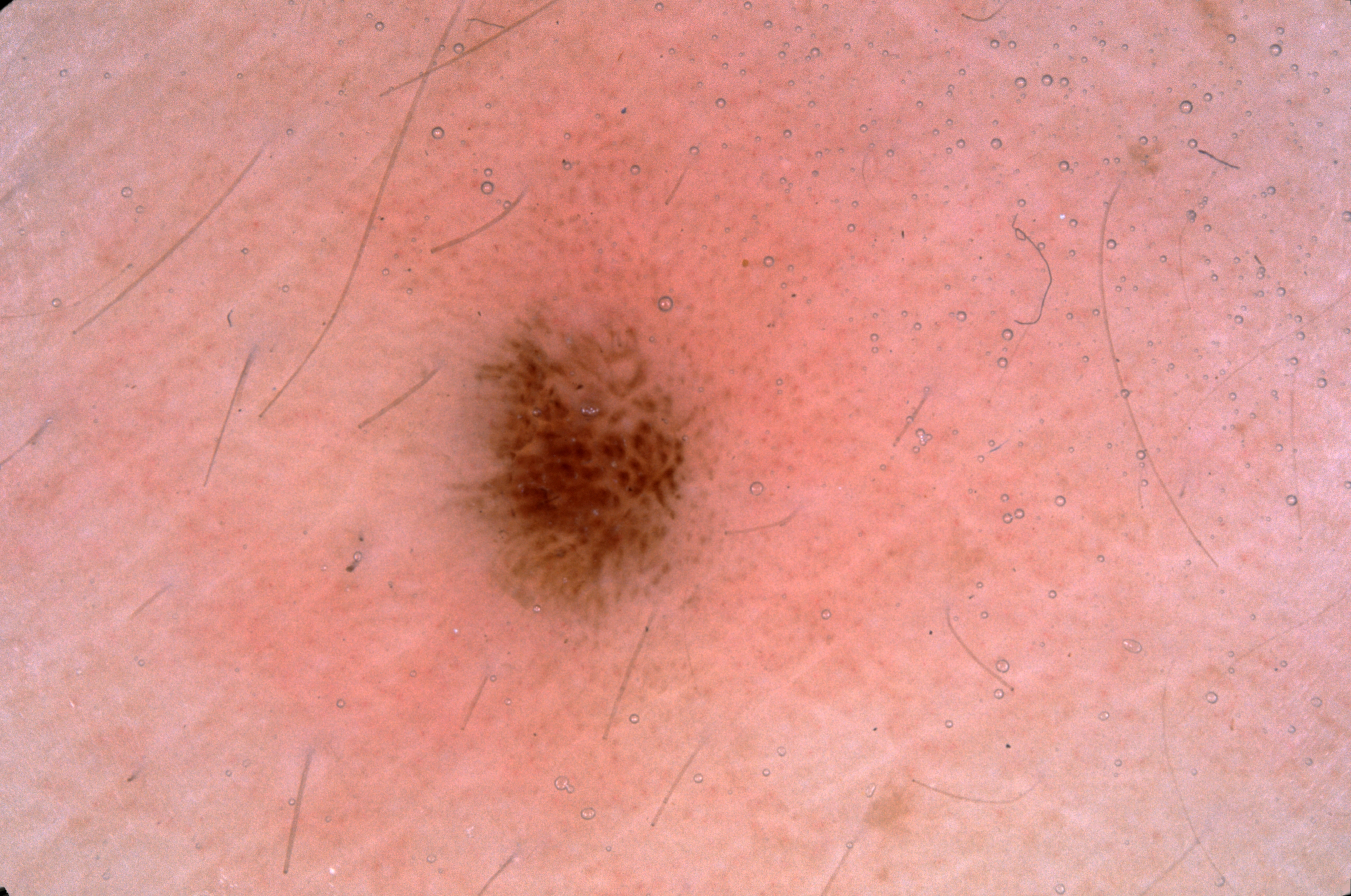<lesion>
  <image>
    <modality>dermoscopy</modality>
  </image>
  <lesion_location>
    <bbox_xyxy>413, 268, 790, 651</bbox_xyxy>
  </lesion_location>
  <diagnosis>
    <name>melanocytic nevus</name>
    <malignancy>benign</malignancy>
    <lineage>melanocytic</lineage>
    <provenance>clinical</provenance>
  </diagnosis>
</lesion>